Dermoscopy of a skin lesion · acquired for a research image collection, with no referral diagnosis:
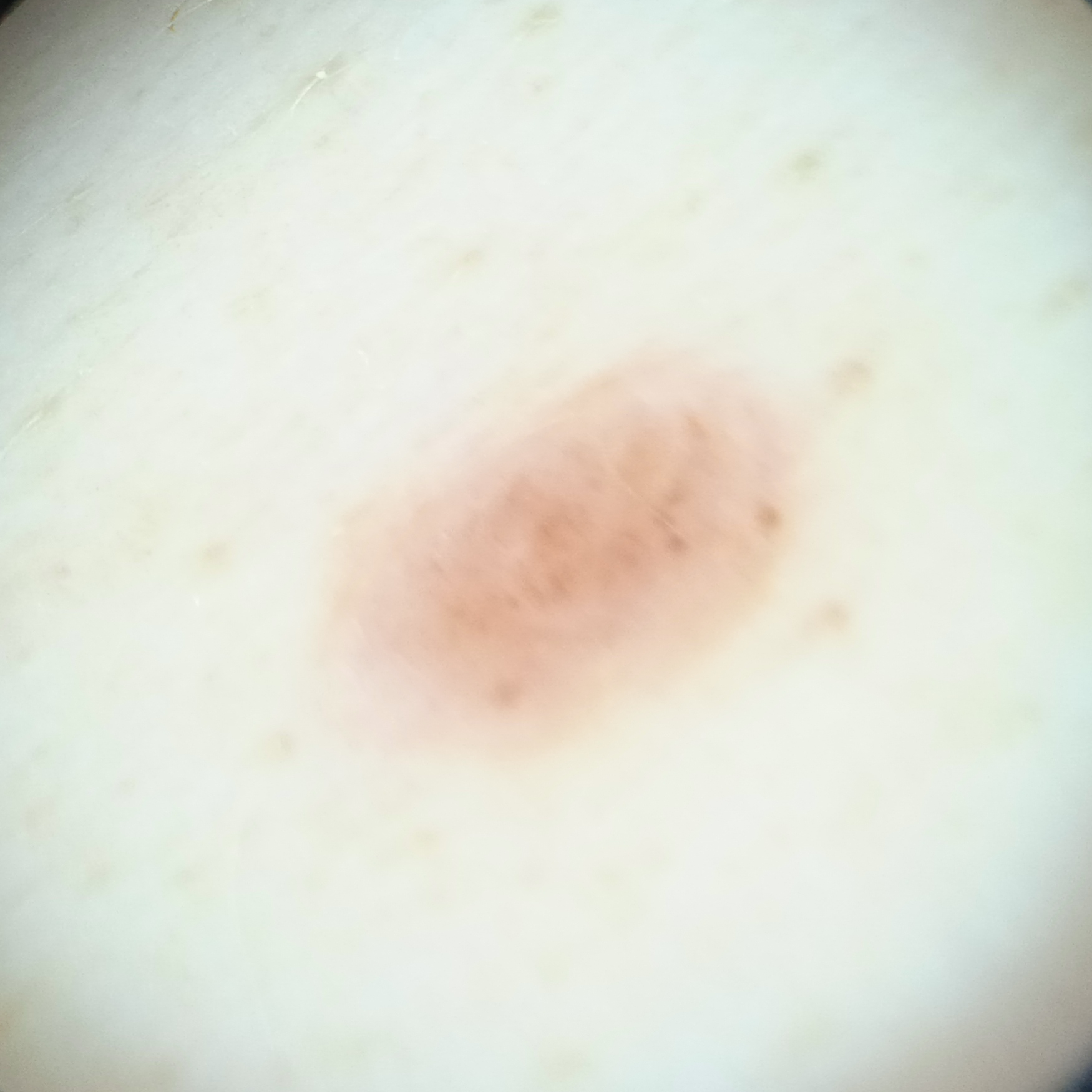Measuring roughly 4.9 mm. The dermatologists' assessment was a melanocytic nevus.